The patient is a female aged 18–29; the affected area is the front of the torso, arm, head or neck and leg; the photograph was taken at a distance:
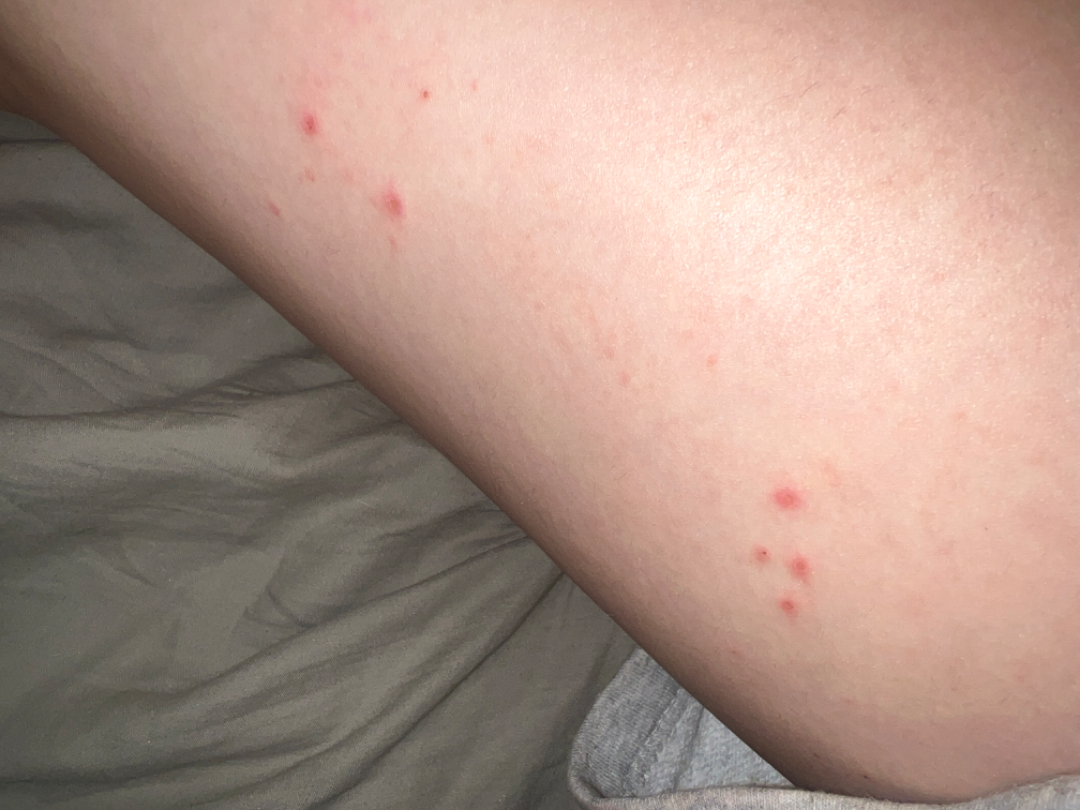patient describes the issue as — a rash
onset — less than one week
described texture — flat
reported symptoms — bleeding and itching
systemic symptoms — none reported
differential diagnosis — favoring Insect Bite; possibly Eczema; also raised was Molluscum Contagiosum; less likely is Allergic Contact Dermatitis; less probable is Abrasion, scrape, or scab